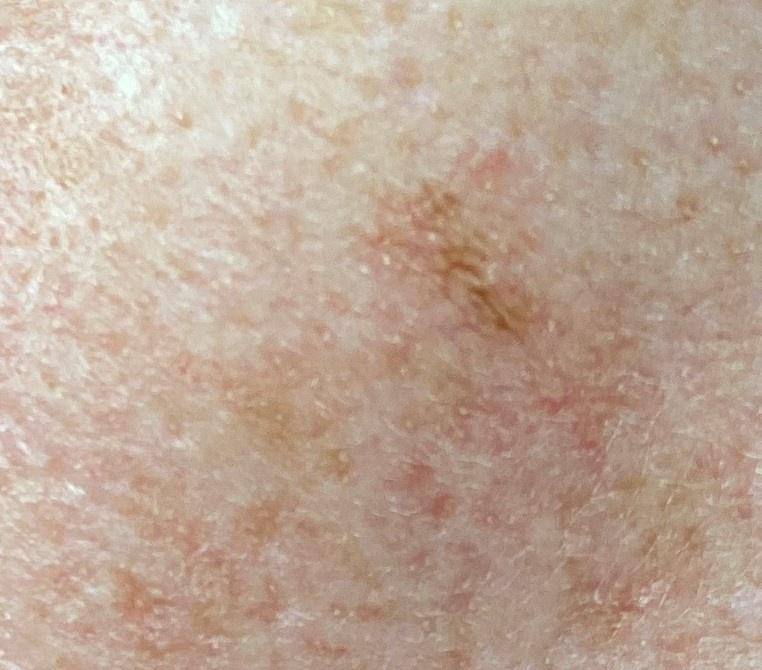Q: What kind of image is this?
A: clinical overview photograph
Q: What is the anatomic site?
A: the head or neck
Q: What is the diagnosis?
A: Solar lentigo